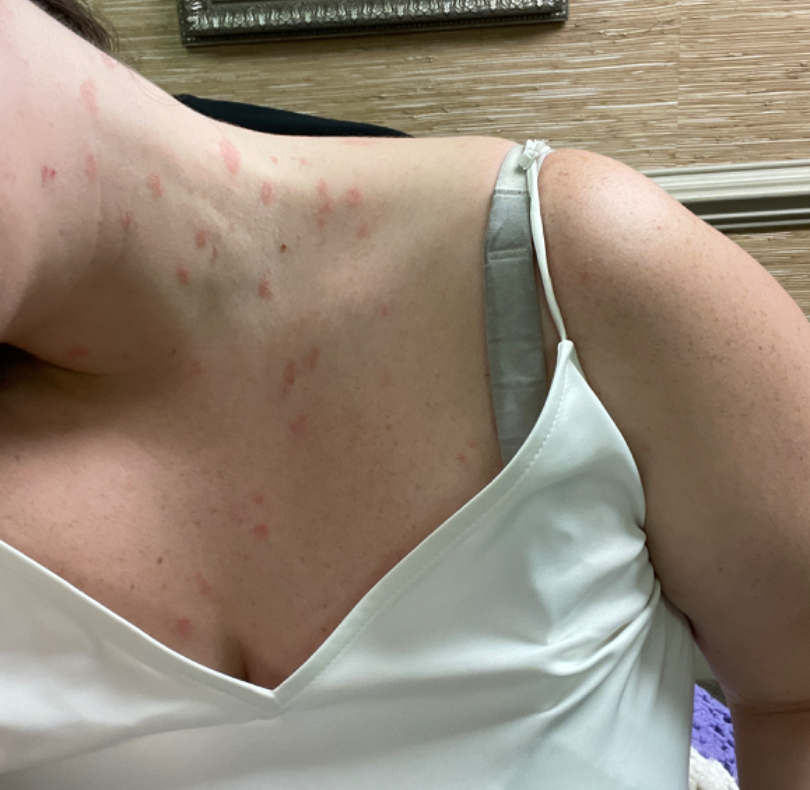surface texture = flat
lesion symptoms = itching
photo taken = at a distance
contributor = female, age 18–29
present for = less than one week
patient's own categorization = a rash
skin tone = FST I; human graders estimated MST 2 or 3 (two reviewer pools)
location = head or neck and front of the torso
clinical impression = Pityriasis rosea (weight 0.67); Psoriasis (weight 0.33)